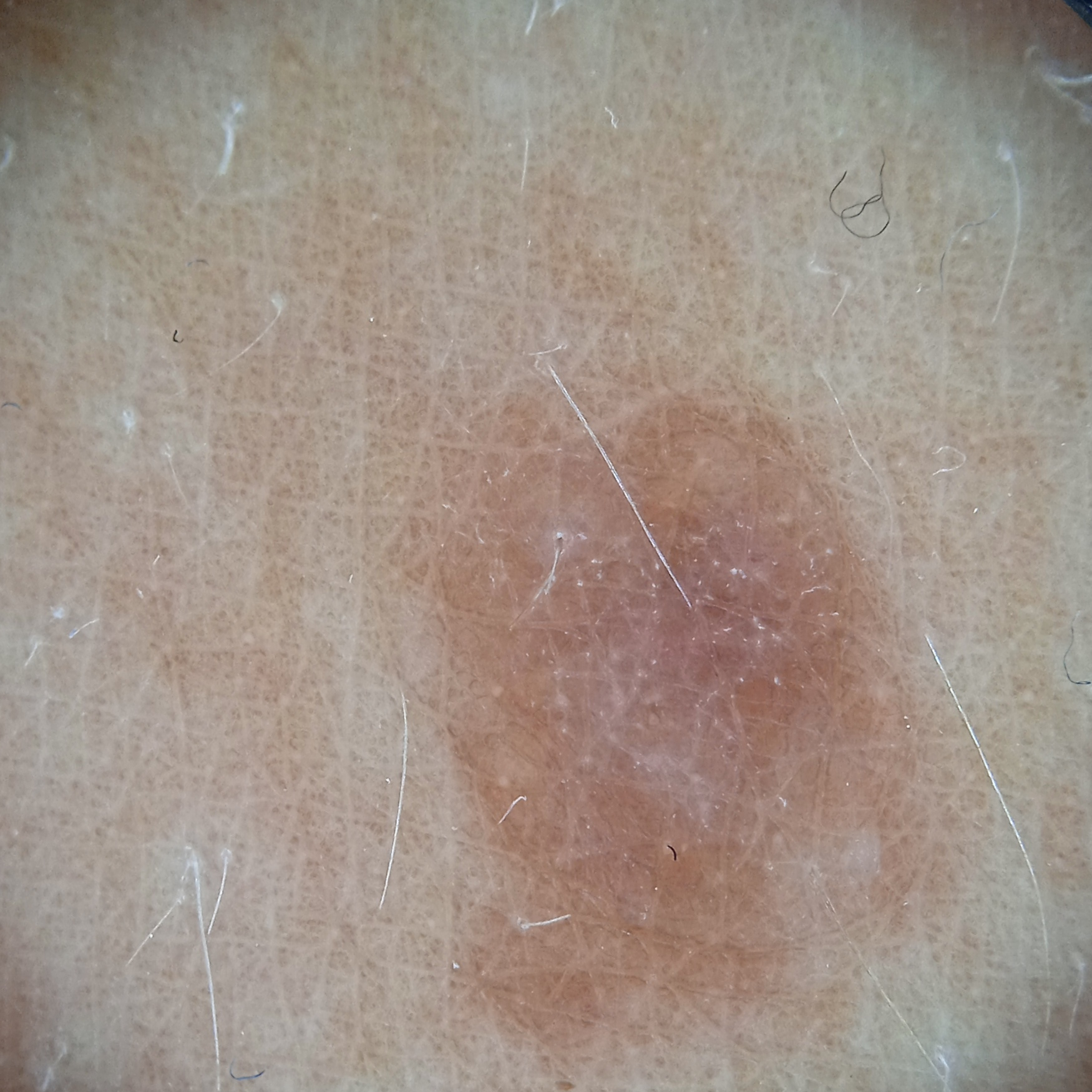The lesion was left diagnostically undetermined on review. <lesion>
<risk_factors>
<positive>a history of sunbed use</positive>
<negative>no immunosuppression</negative>
</risk_factors>
<patient>
<age>47</age>
<sex>female</sex>
</patient>
<sun_reaction>skin tans without first burning</sun_reaction>
<image>dermoscopy</image>
<mole_burden>a moderate number of melanocytic nevi</mole_burden>
<referral>research study (no referral diagnosis)</referral>
<lesion_location>an arm</lesion_location>
<lesion_size>
<diameter_mm>8.1</diameter_mm>
</lesion_size>
</lesion>